A skin lesion imaged with a dermatoscope — 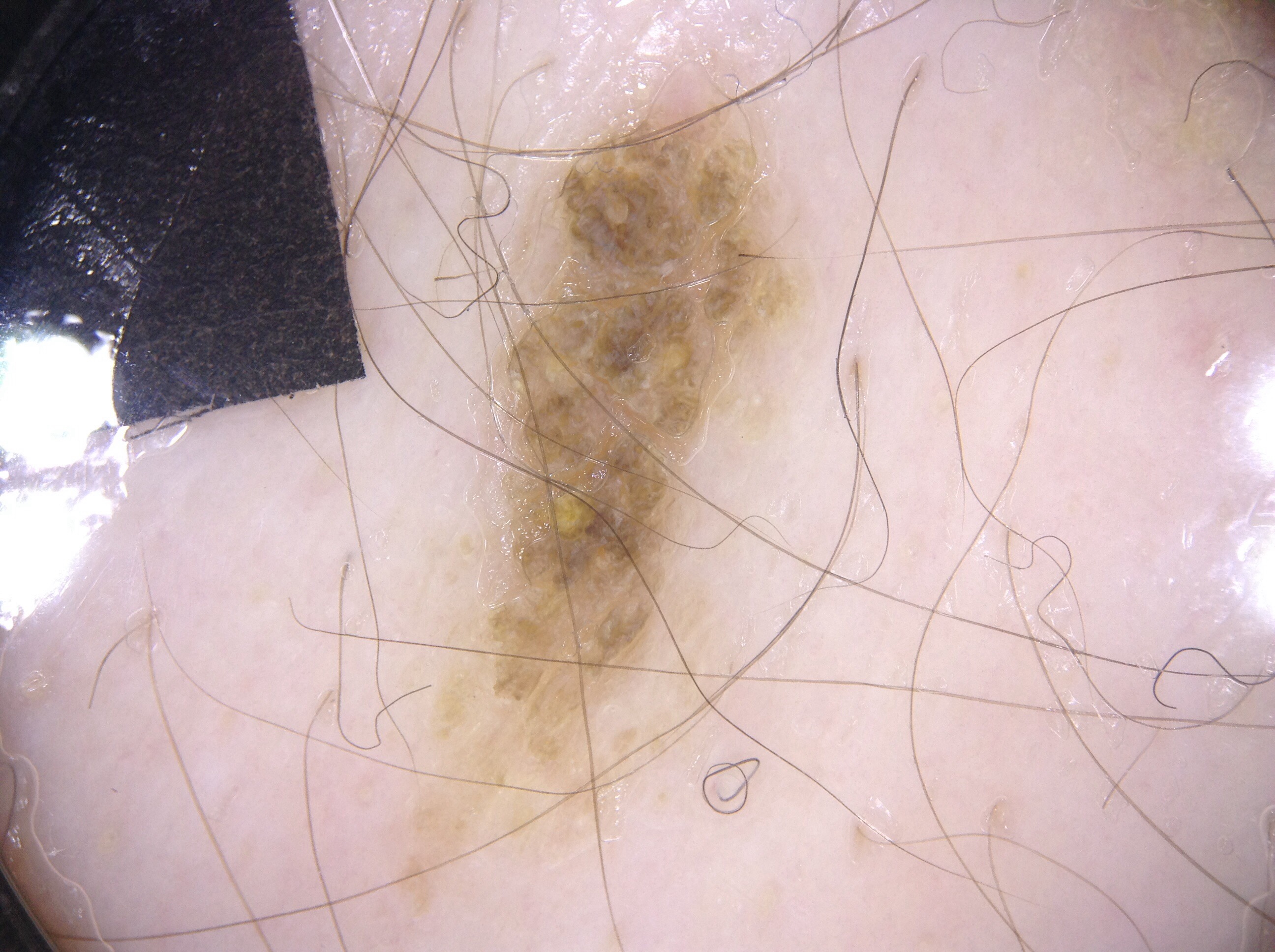The lesion occupies roughly 18% of the field.
On dermoscopy, the lesion shows no pigment network, negative network, milia-like cysts, or streaks.
The visible lesion spans bbox=[388, 40, 817, 913].
Diagnosed as a seborrheic keratosis, a benign lesion.